A dermoscopic image of a skin lesion.
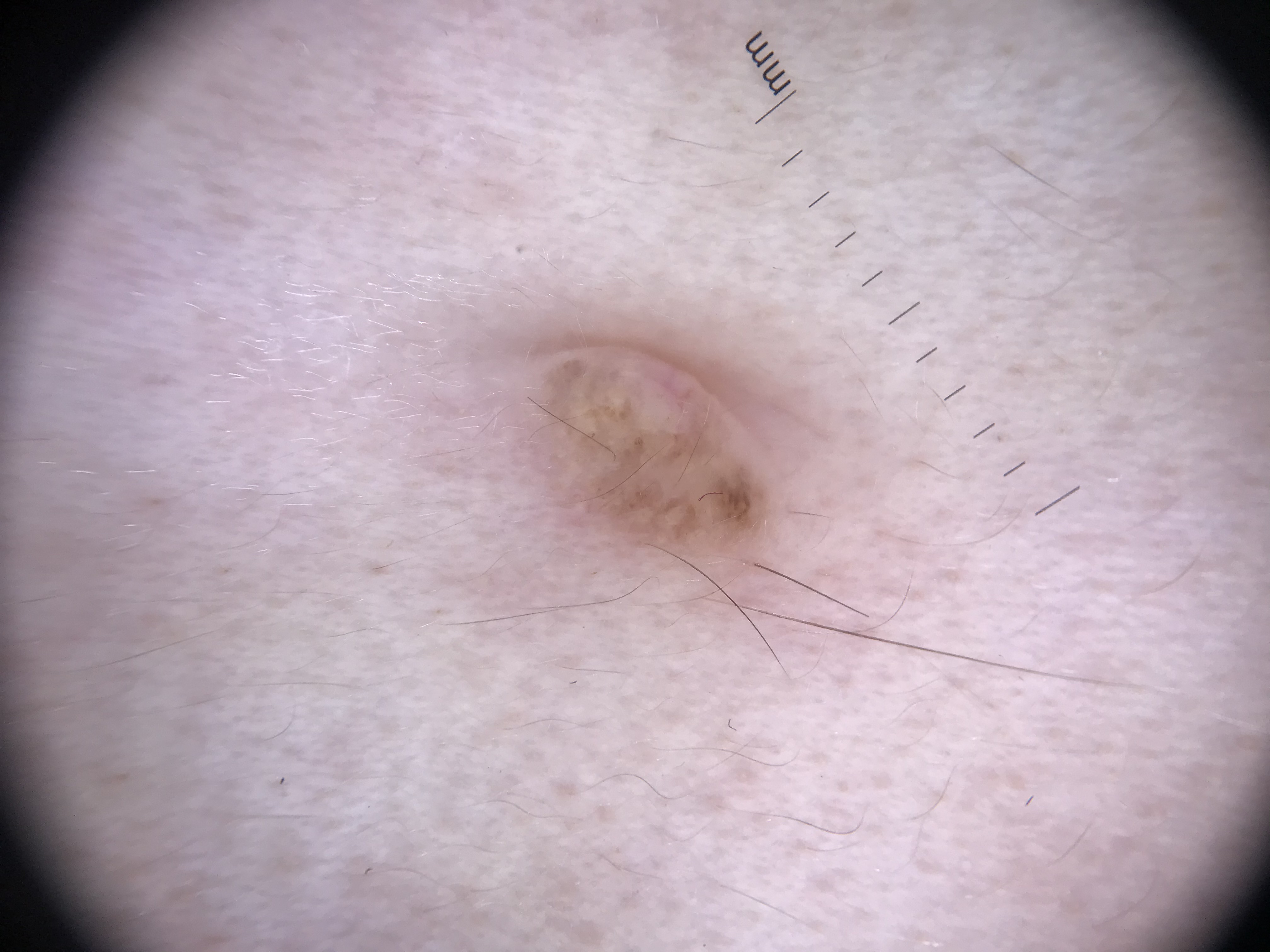class=dermal nevus (expert consensus).